The contributor is 18–29, female; the affected area is the arm, back of the torso, head or neck, back of the hand, front of the torso and palm; this image was taken at an angle: 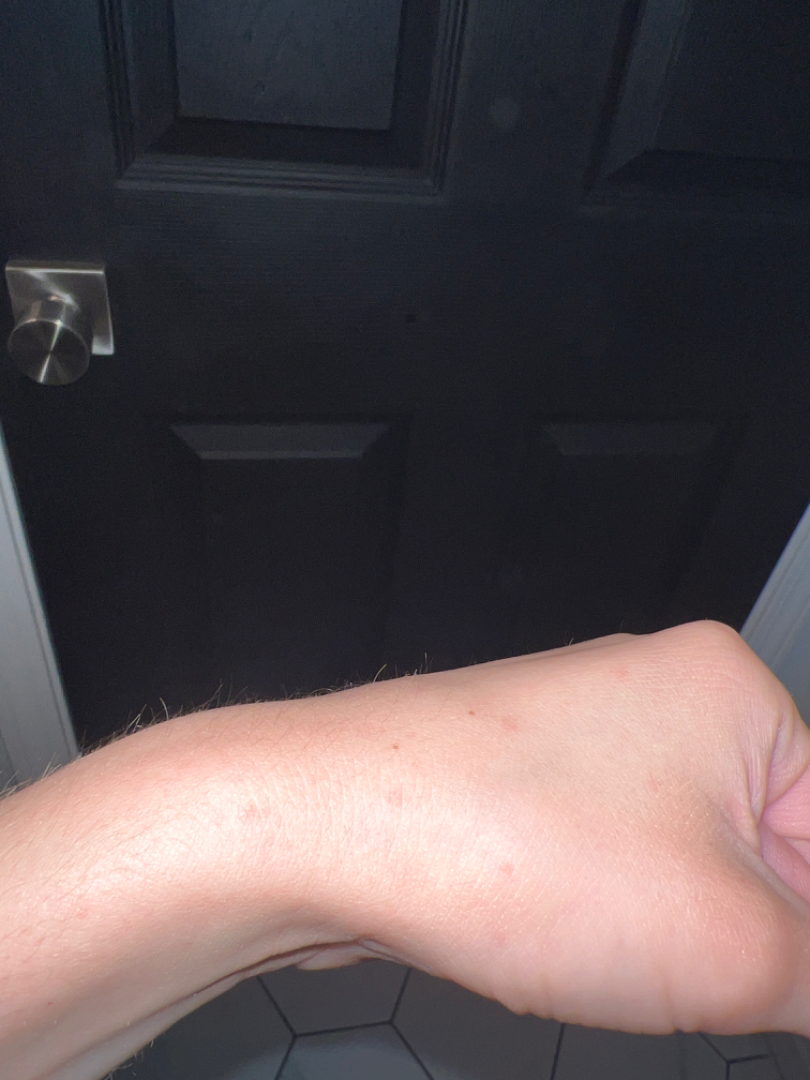described texture=flat and raised or bumpy | patient describes the issue as=a rash | onset=about one day | skin tone=Fitzpatrick skin type II | patient-reported symptoms=itching, bothersome appearance and burning | clinical impression=most consistent with Insect Bite.